The chart notes prior malignancy (patient or family), prior skin cancer (patient or family), and no tobacco use; a male subject in their 70s — 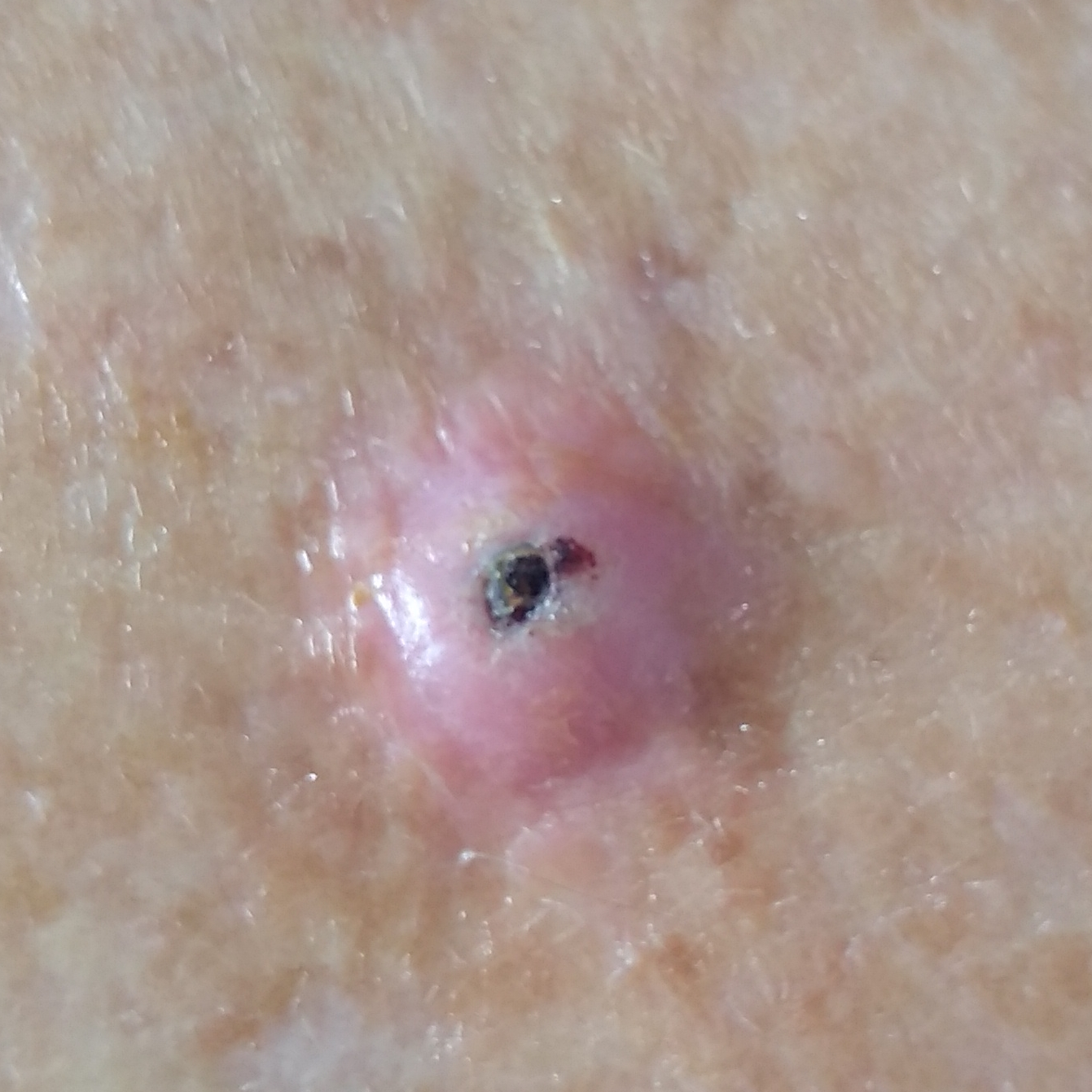Findings:
- location — a thigh
- patient-reported symptoms — elevation, itching, bleeding / no pain
- pathology — squamous cell carcinoma (biopsy-proven)